A dermoscopic close-up of a skin lesion.
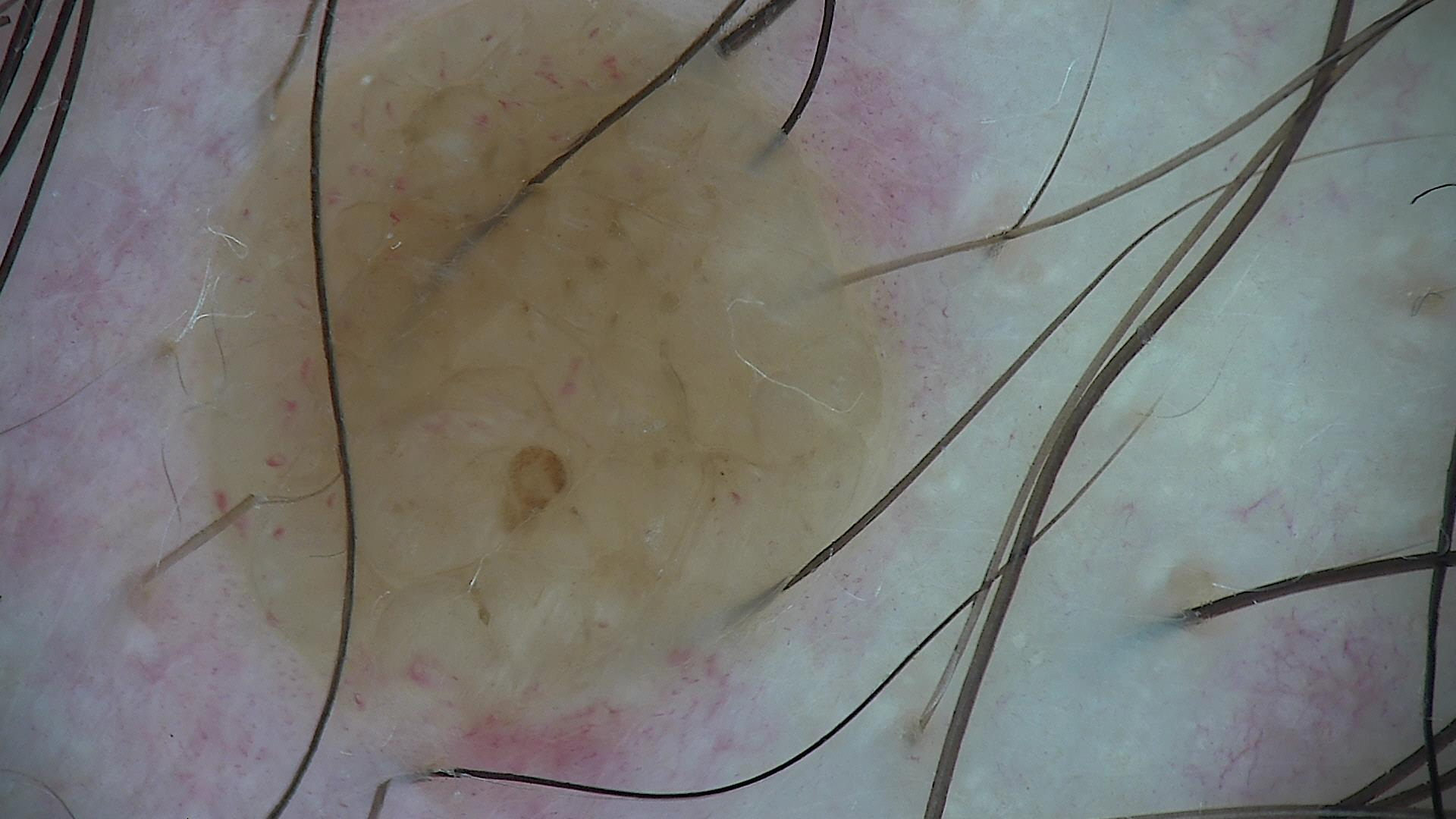The diagnostic label was a banal lesion — a dermal nevus.